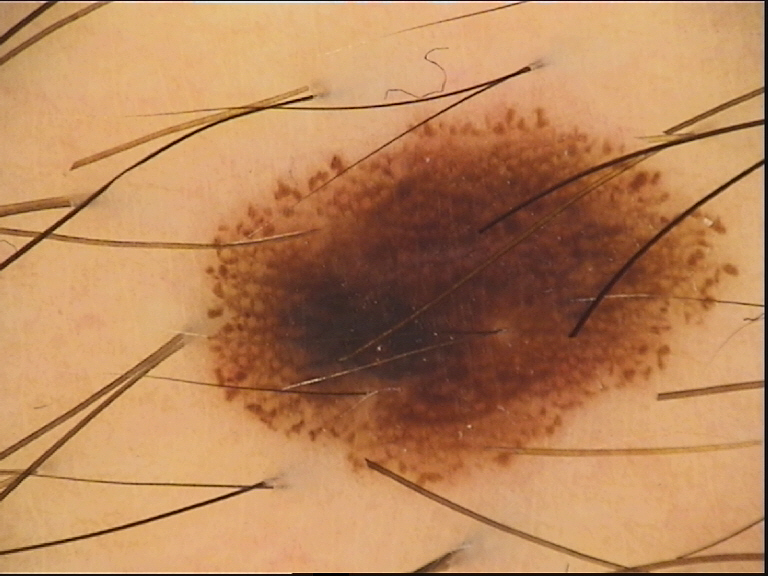class — dysplastic compound nevus (expert consensus)